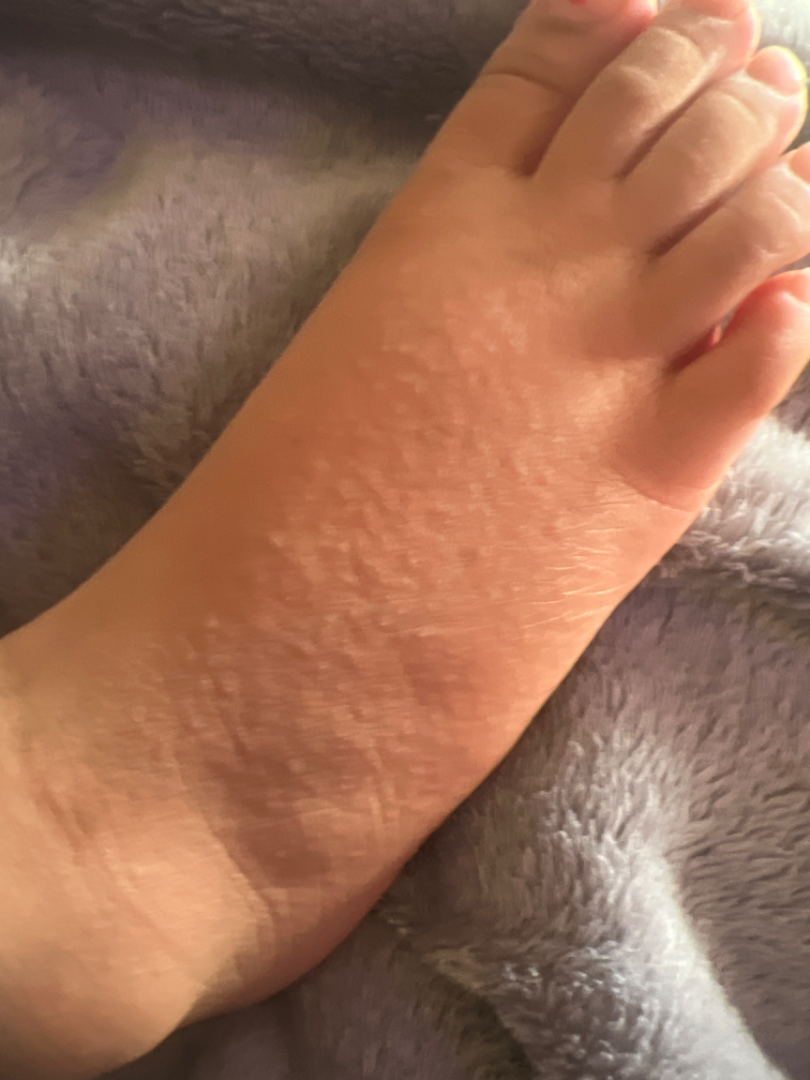The lesion involves the leg and top or side of the foot. Present for less than one week. The patient notes the lesion is raised or bumpy. Female patient, age 18–29. Self-categorized by the patient as a rash. The patient reported no systemic symptoms. This is a close-up image. Symptoms reported: itching. One reviewing dermatologist: most consistent with Acrokeratosis verruciformis; with consideration of Granuloma annulare; also raised was Keratoderma.